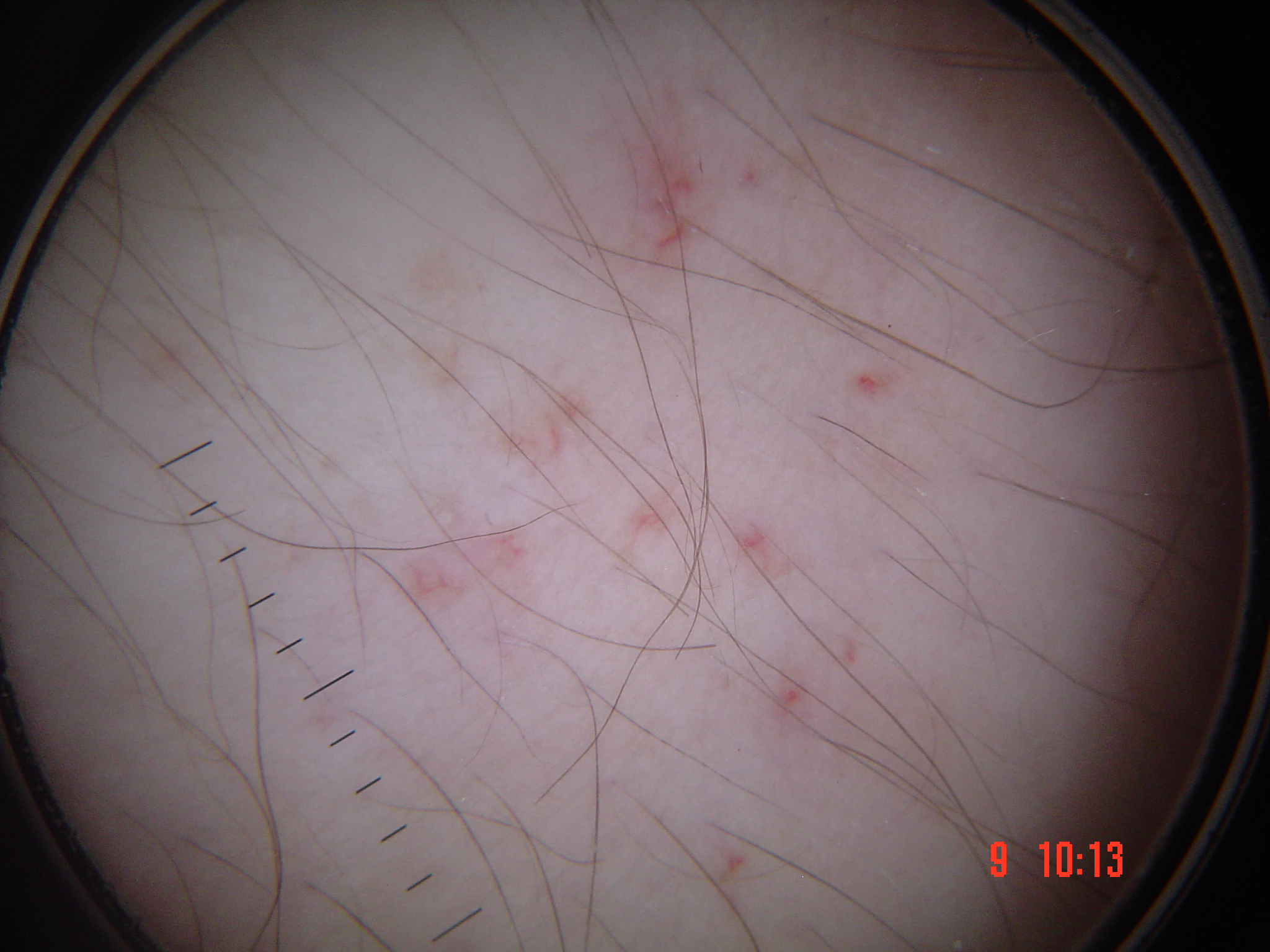imaging = dermoscopy; diagnosis = spider angioma (expert consensus).